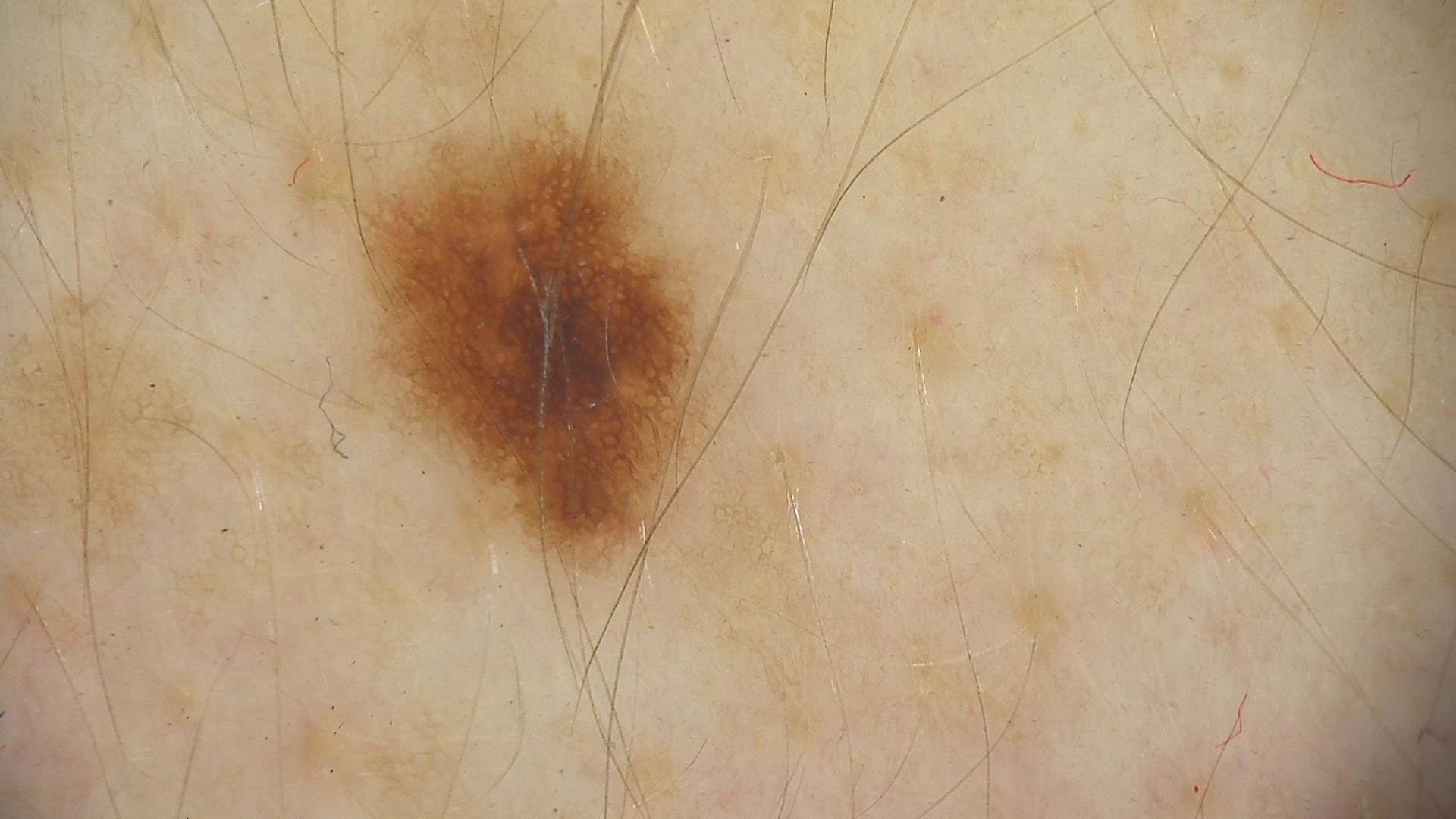Summary: A dermoscopic image of a skin lesion. Conclusion: Diagnosed as a dysplastic junctional nevus.